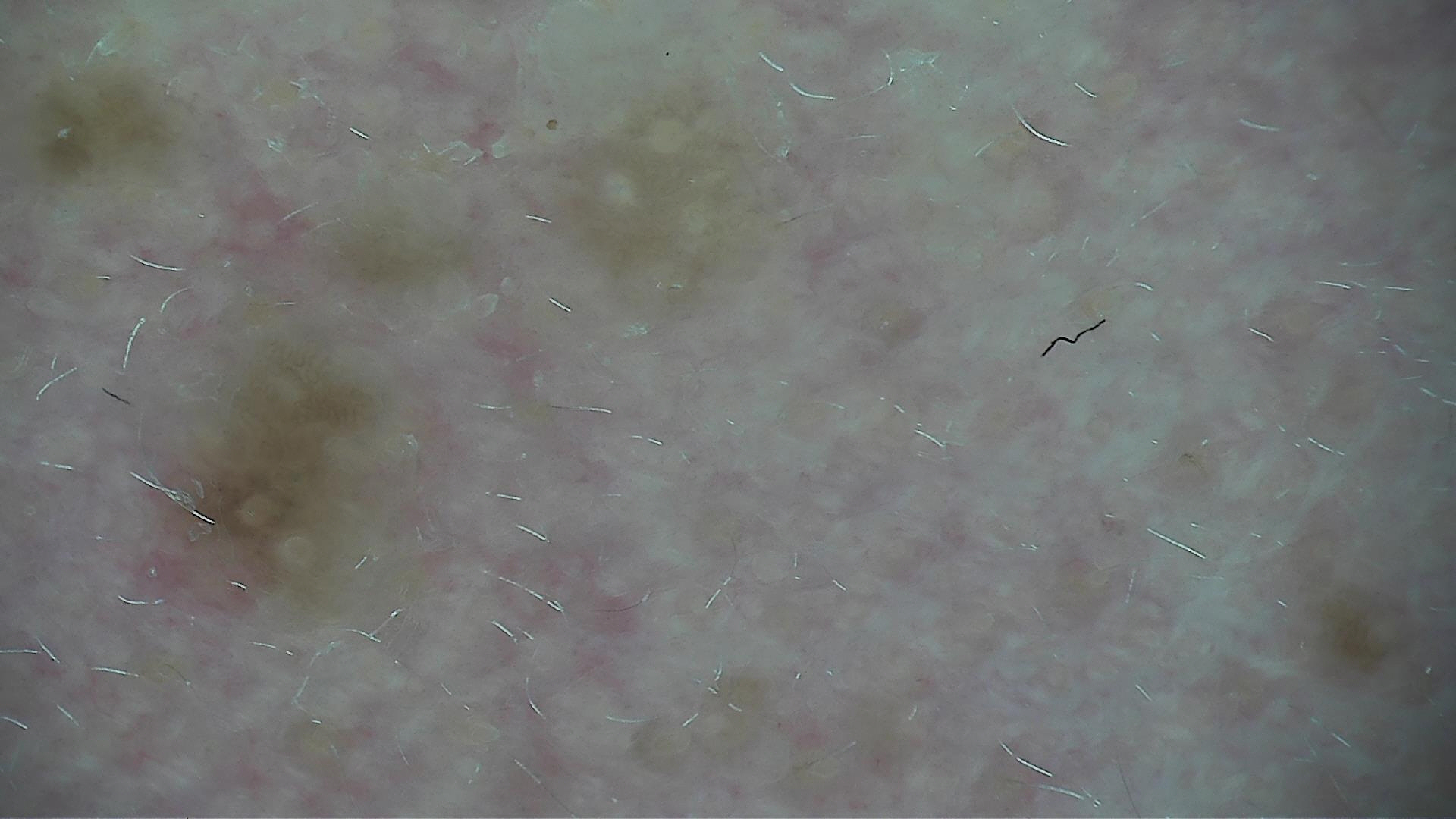Findings:
• image · dermatoscopy
• diagnosis · seborrheic keratosis (expert consensus)